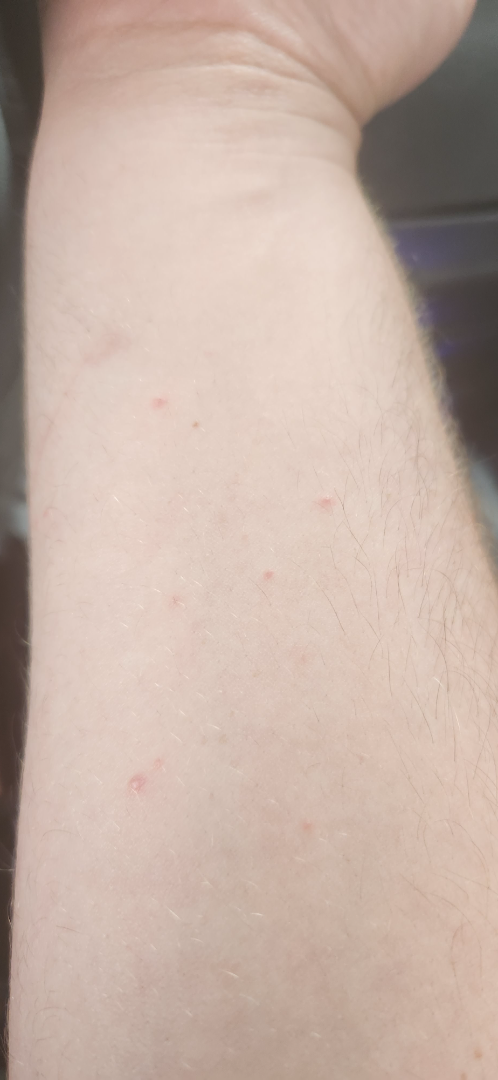assessment: could not be assessed | shot type: close-up | patient: male, age 18–29 | patient's own categorization: a rash | skin tone: FST II; lay reviewers estimated Monk skin tone scale 1 or 2 | associated systemic symptoms: none reported | location: arm | history: less than one week | symptoms: bothersome appearance and itching.